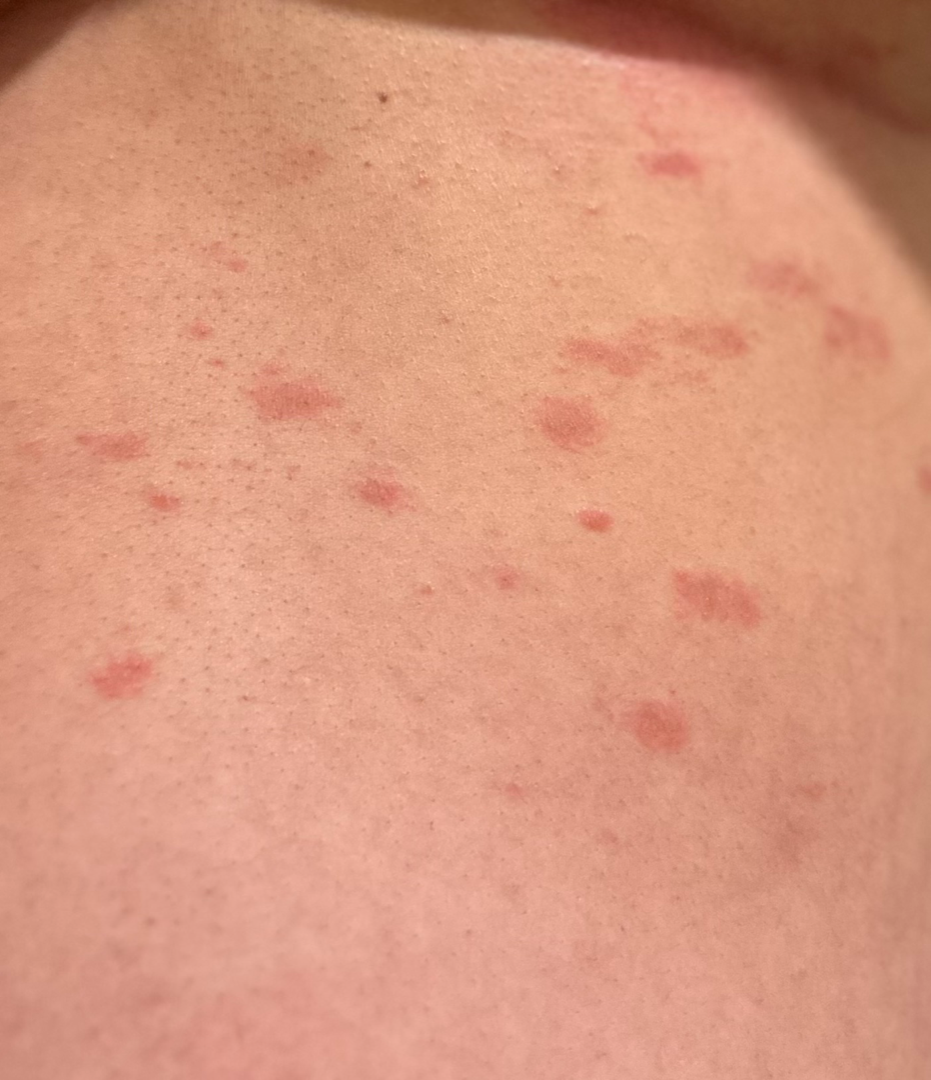Patient information:
Close-up view.
Review:
Reviewed remotely by one dermatologist: most likely Pityriasis rosea; also raised was Lichen planus/lichenoid eruption; a remote consideration is Syphilis.